This image was taken at an angle — 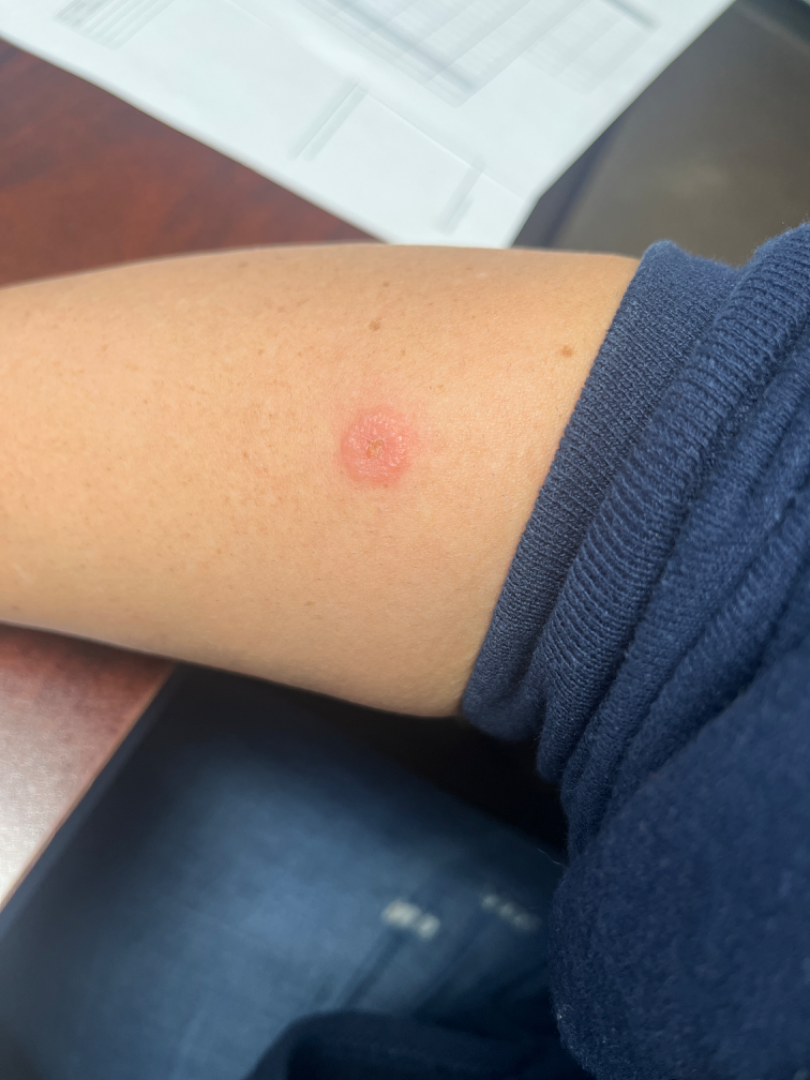The reviewing dermatologist was unable to assign a differential diagnosis from the image.
Texture is reported as raised or bumpy and rough or flaky.
Fitzpatrick III.